The arm is involved. The photograph is a close-up of the affected area. The contributor is male — 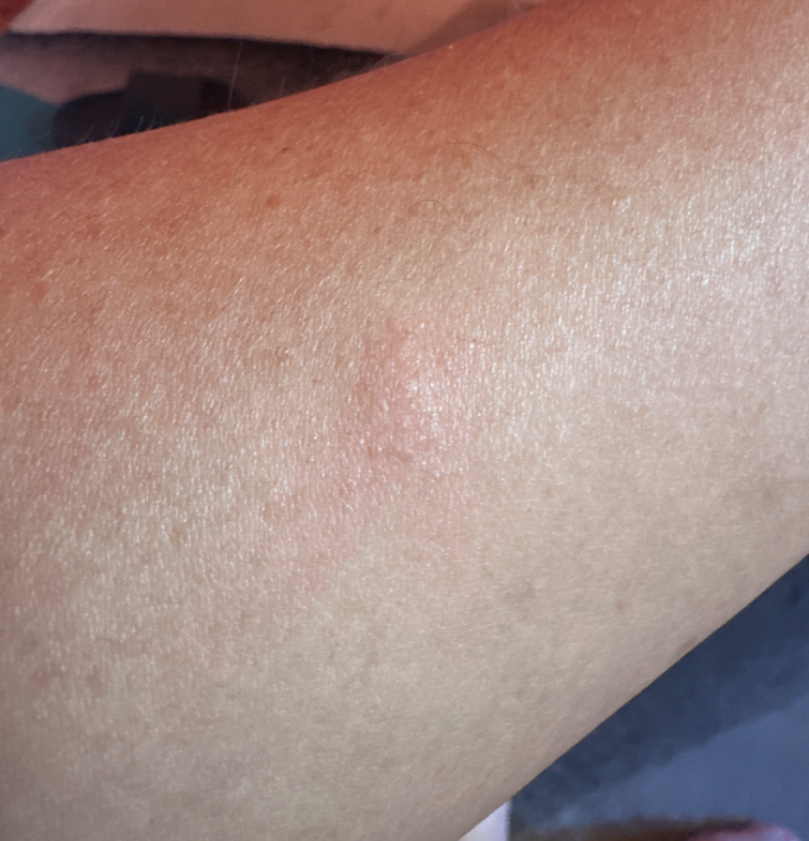Urticaria (possible); Insect Bite (possible); Cyst (possible).